The photo was captured at a distance · the patient notes the lesion is raised or bumpy and rough or flaky · symptoms reported: itching, burning and pain · located on the palm: 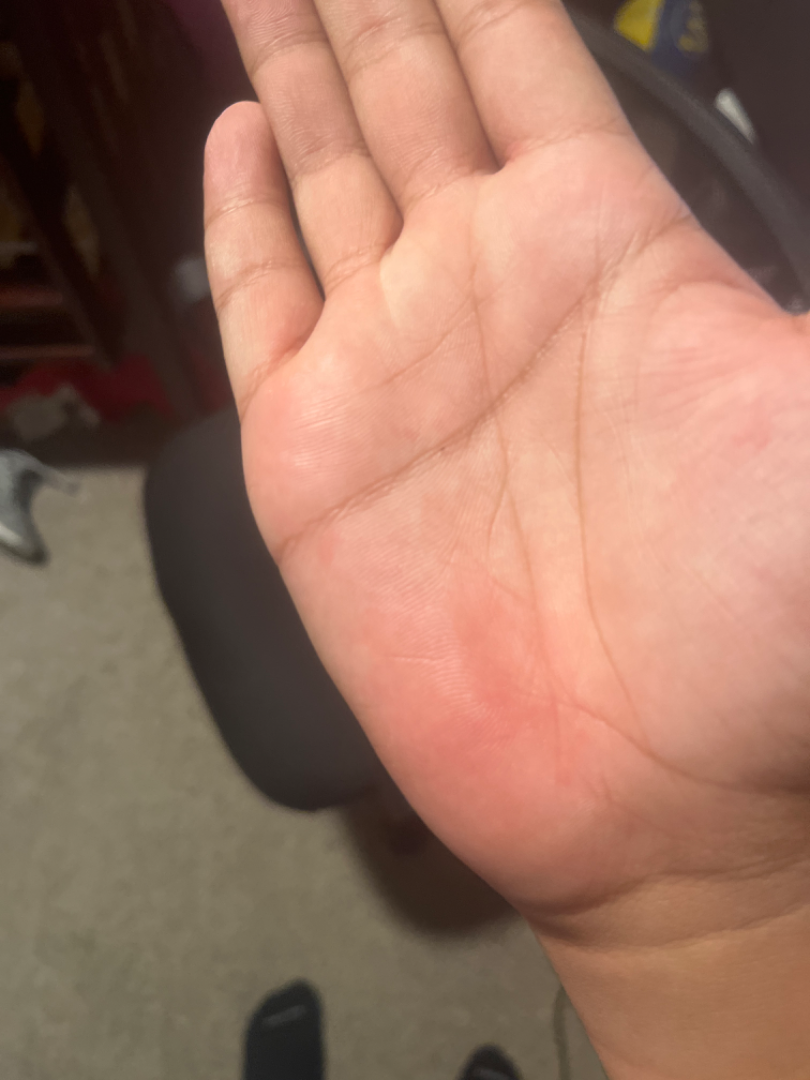Findings:
• assessment · not assessable